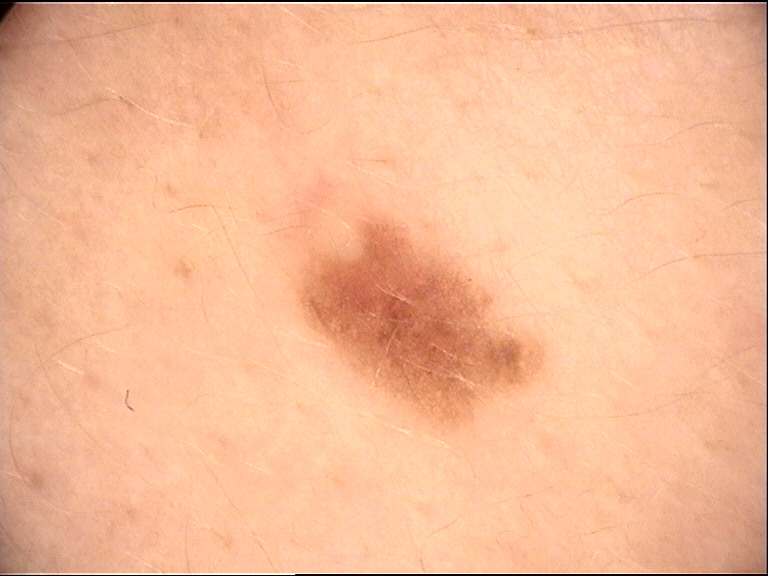Conclusion: The diagnostic label was a dysplastic junctional nevus.